The condition has been present for one to four weeks, the photograph was taken at an angle, the patient is a female aged 18–29, the patient indicates itching and bothersome appearance, self-categorized by the patient as a rash, the affected area is the arm, Fitzpatrick phototype III; lay reviewers estimated MST 3 or 4 (two reviewer pools), texture is reported as raised or bumpy and fluid-filled: 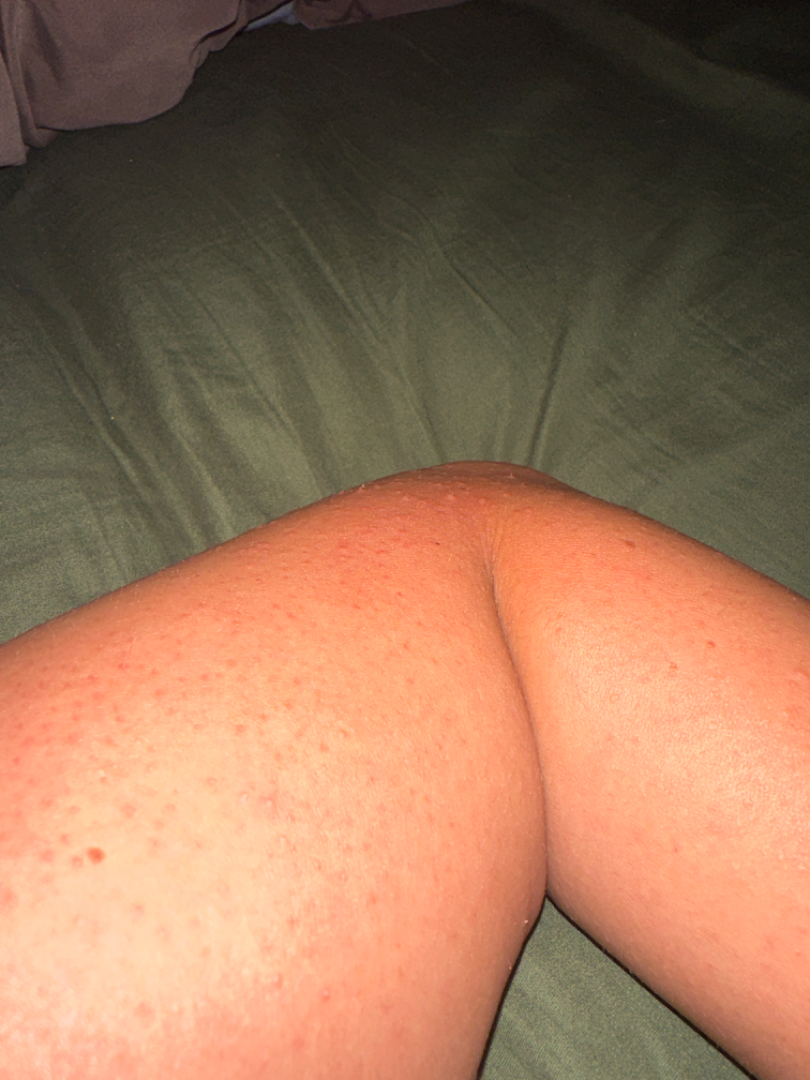| feature | finding |
|---|---|
| impression | Acute dermatitis, NOS (primary) |